A skin lesion imaged with a dermatoscope:
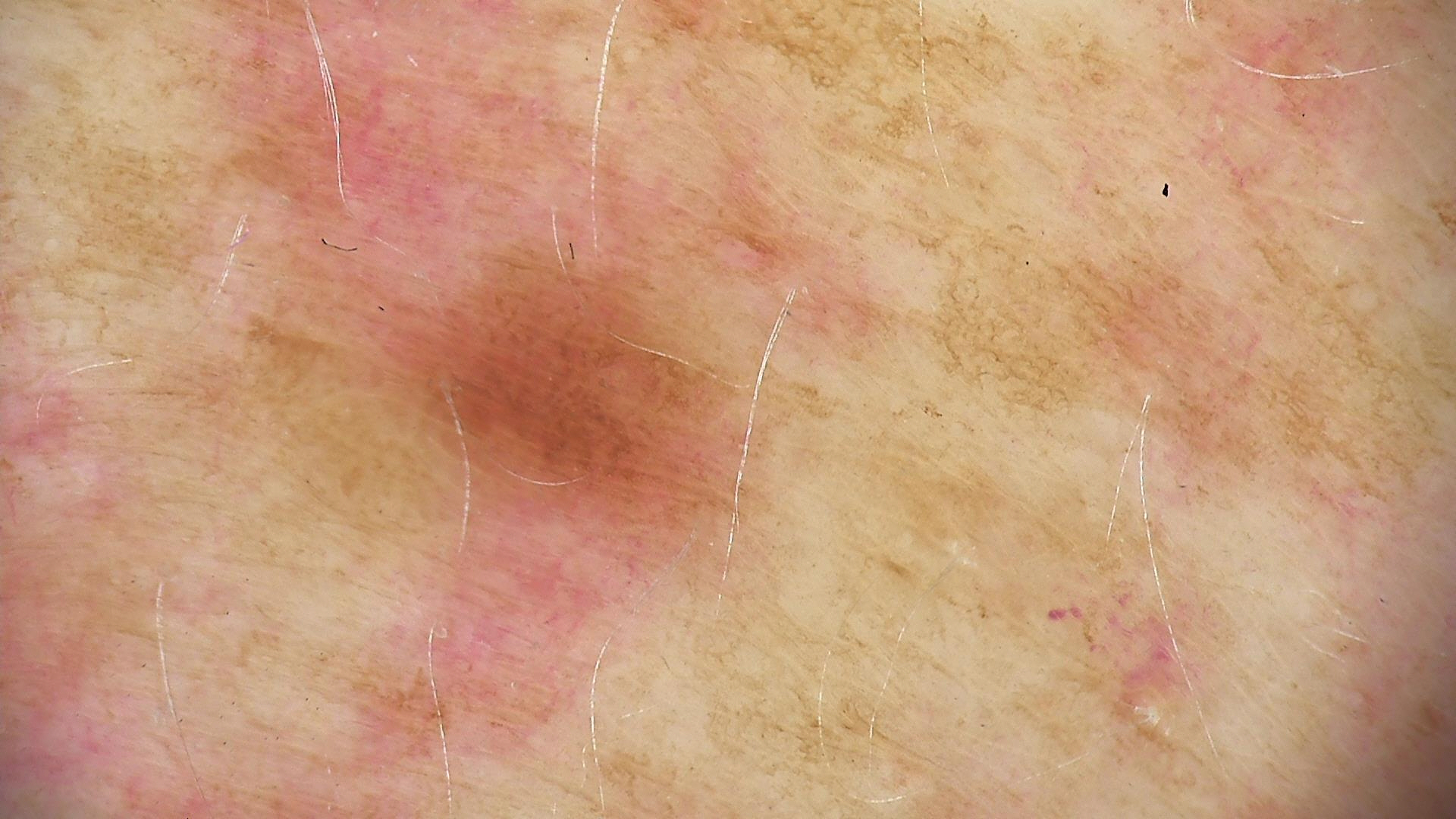<case>
  <diagnosis>
    <name>dysplastic junctional nevus</name>
    <code>jd</code>
    <malignancy>benign</malignancy>
    <super_class>melanocytic</super_class>
    <confirmation>expert consensus</confirmation>
  </diagnosis>
</case>